A dermoscopy image of a skin lesion; the patient says their skin reddens painfully with sun exposure; acquired for a research image collection, with no referral diagnosis; the patient reports no personal history of skin cancer and no sunbed use; a female patient aged 81.
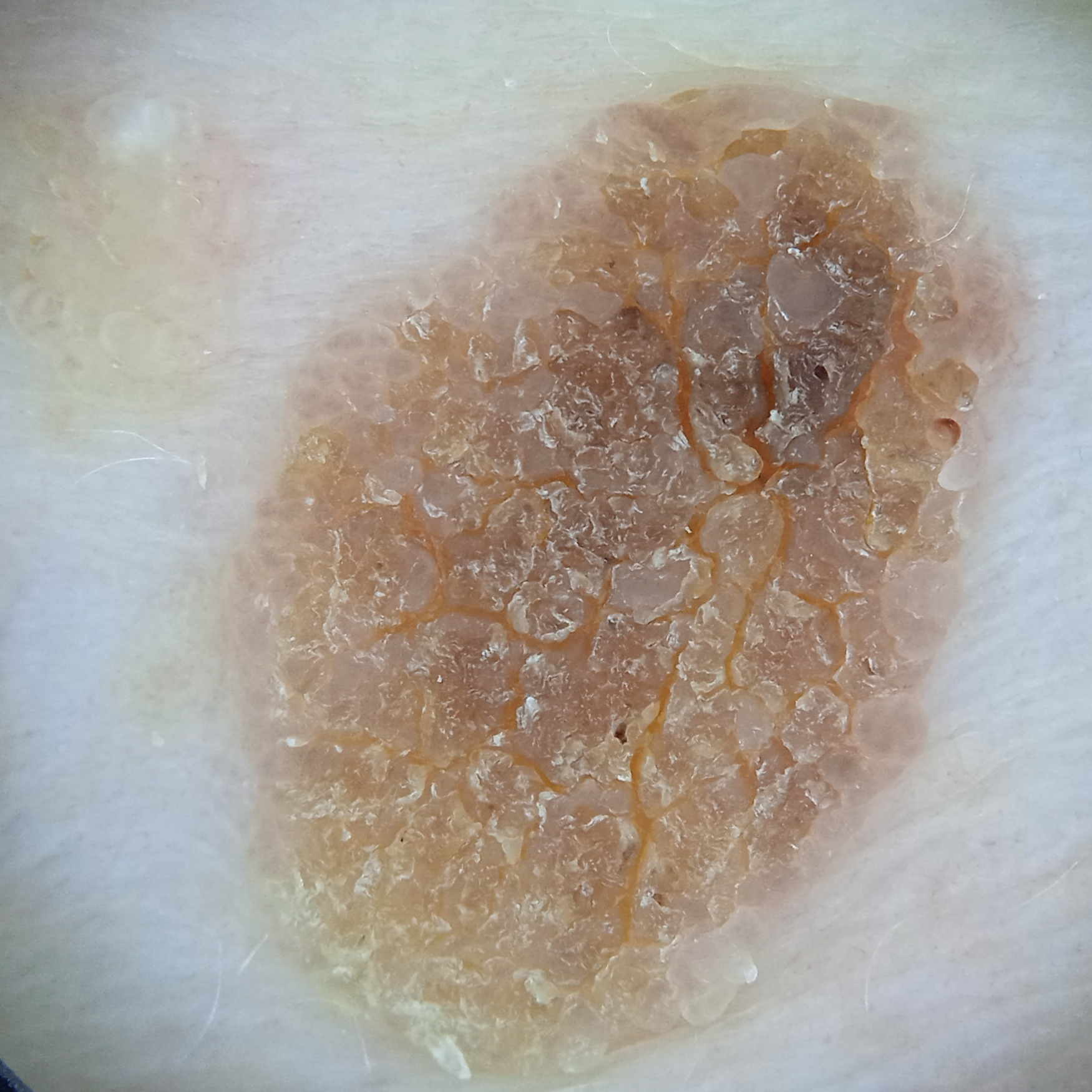• anatomic site: the torso
• diameter: 12.2 mm
• diagnostic label: seborrheic keratosis (dermatologist consensus)